Dermoscopy of a skin lesion: 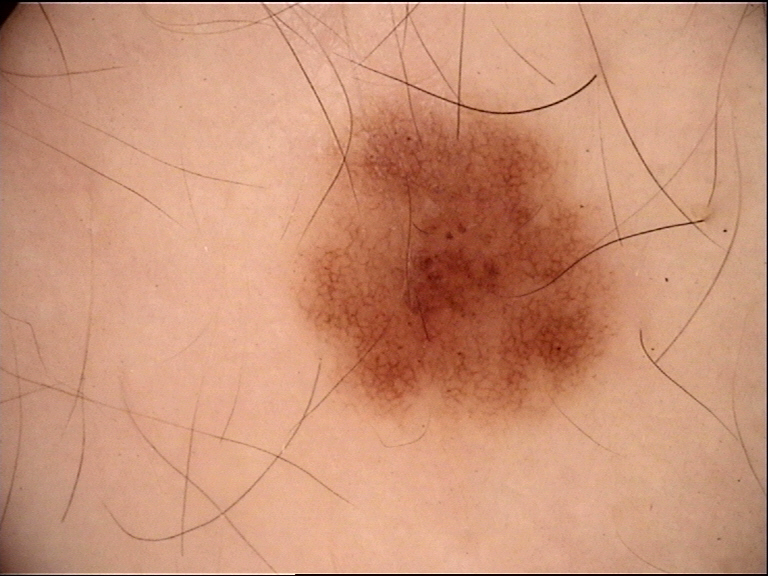Impression:
Labeled as a benign lesion — a dysplastic junctional nevus.